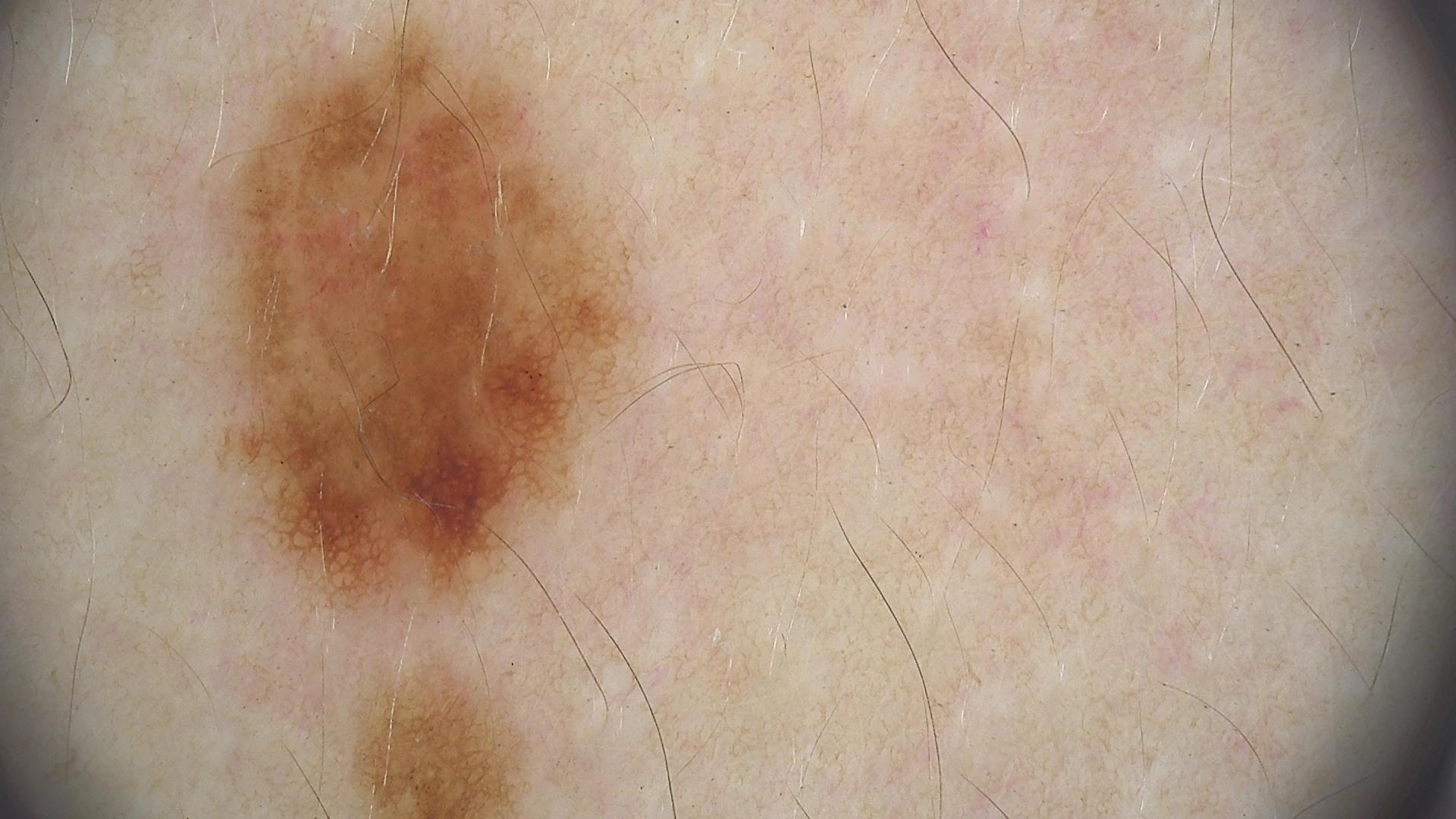| feature | finding |
|---|---|
| image type | dermatoscopy |
| class | dysplastic junctional nevus (expert consensus) |